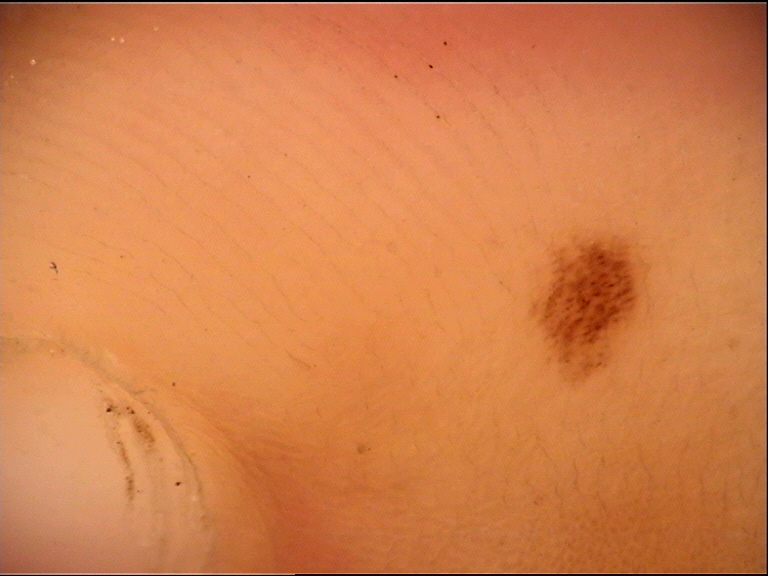diagnosis = acral dysplastic junctional nevus (expert consensus).